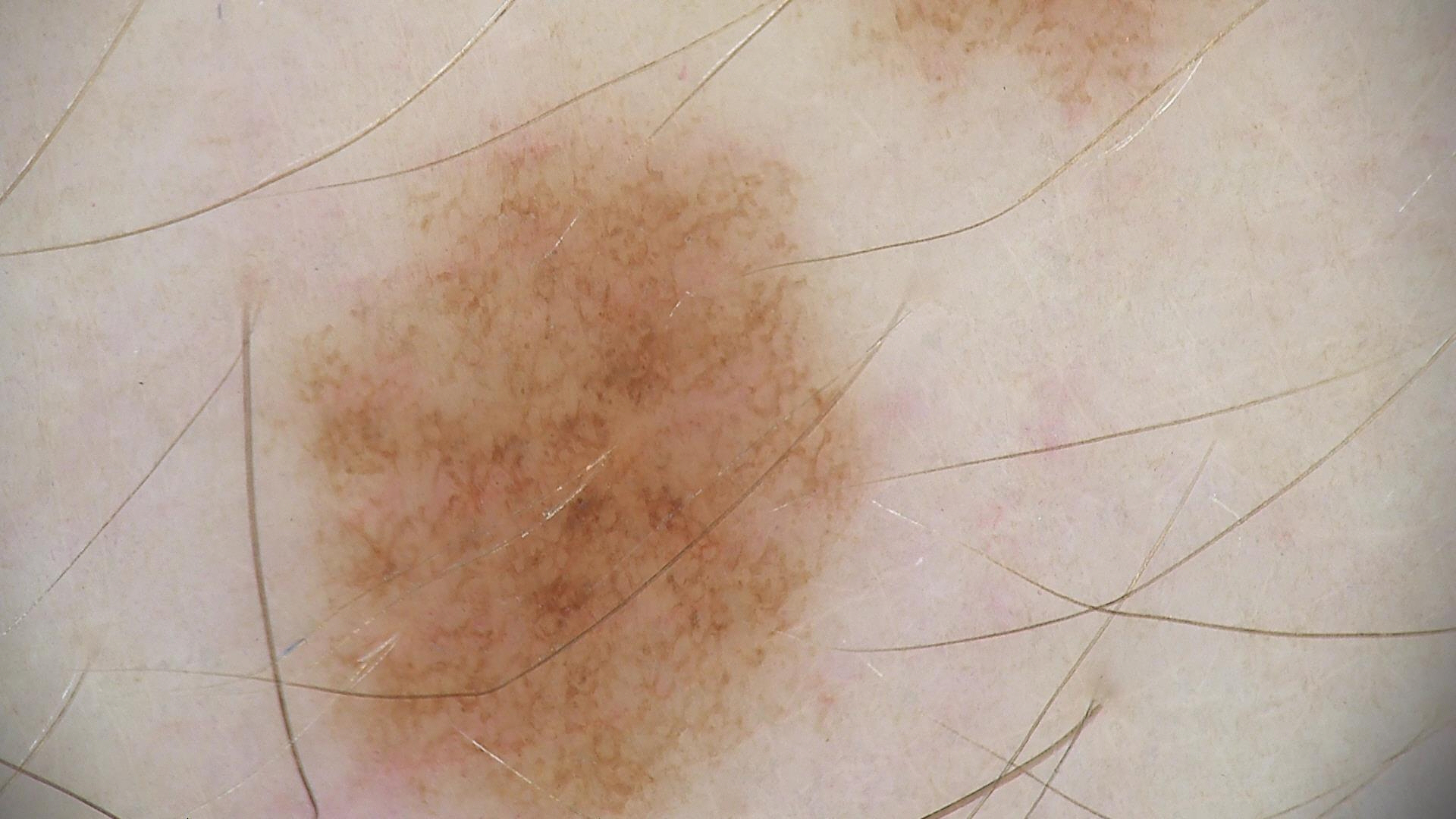Case:
A dermoscopic image of a skin lesion.
Impression:
Consistent with a benign lesion — a dysplastic junctional nevus.